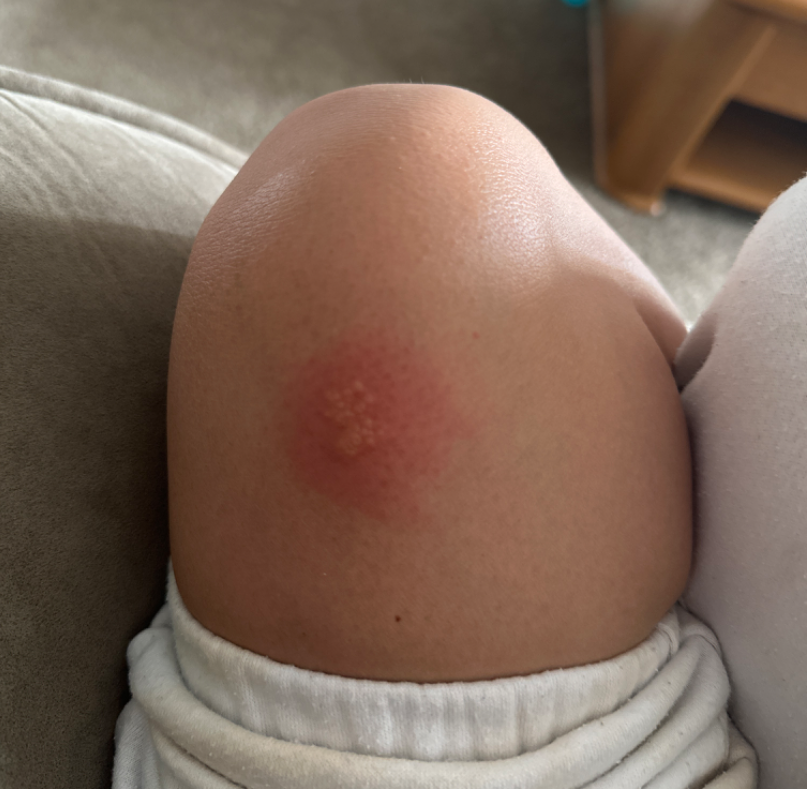| field | value |
|---|---|
| patient's own categorization | a rash |
| symptoms | enlargement and itching |
| skin tone | Fitzpatrick phototype III |
| affected area | leg |
| view | at a distance |
| described texture | raised or bumpy |
| patient | female, age 18–29 |
| duration | more than one year |
| dermatologist impression | Herpes Simplex (primary) |